A skin lesion imaged with a dermatoscope: 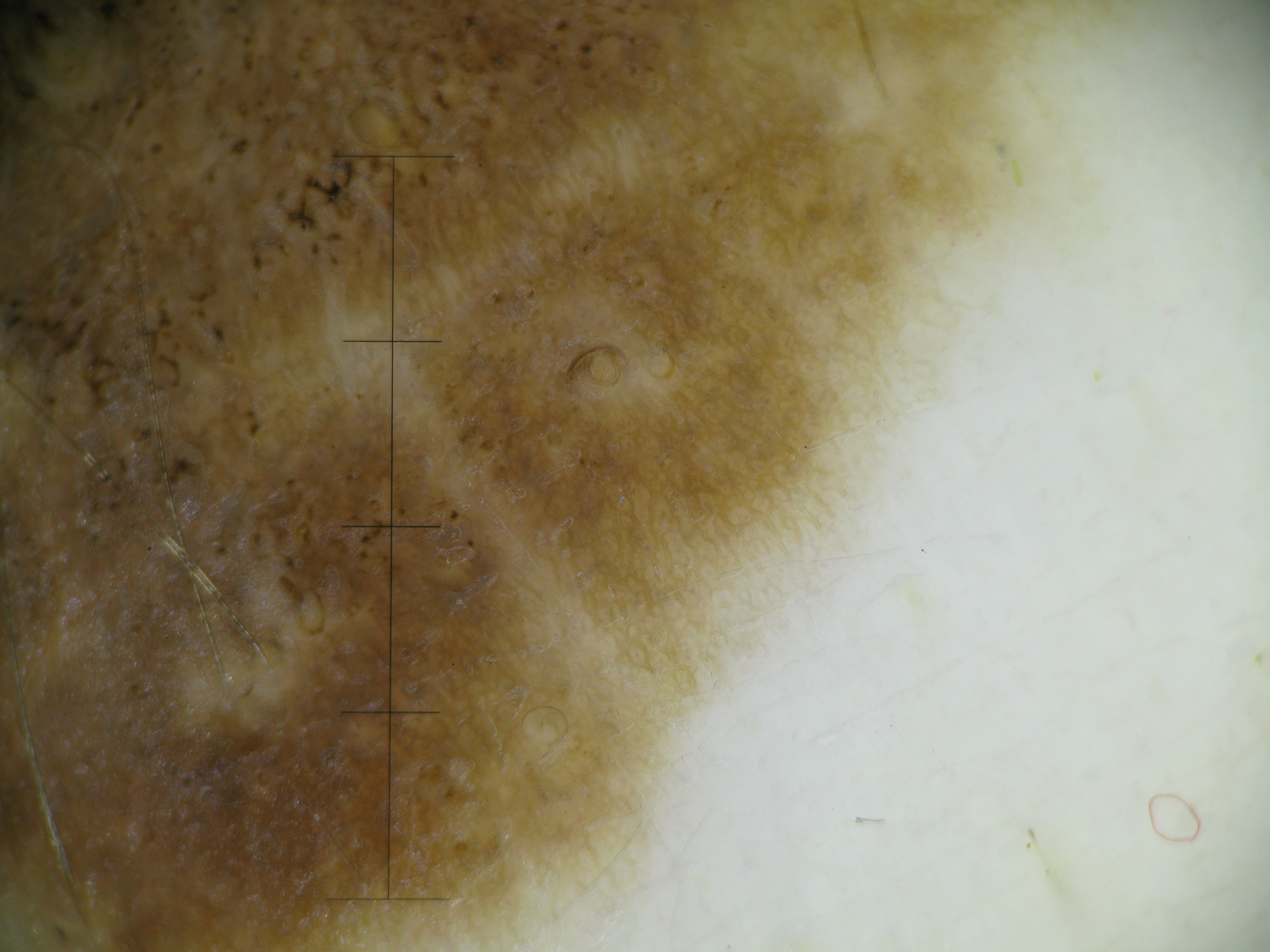The architecture is that of a banal lesion. The diagnosis was a congenital compound nevus.